A male patient age 72. The patient reports a personal history of cancer. Few moles overall by the patient's own estimate. The patient says their skin reddens with sun exposure. A dermoscopy image of a skin lesion. Acquired for a research image collection, with no referral diagnosis: 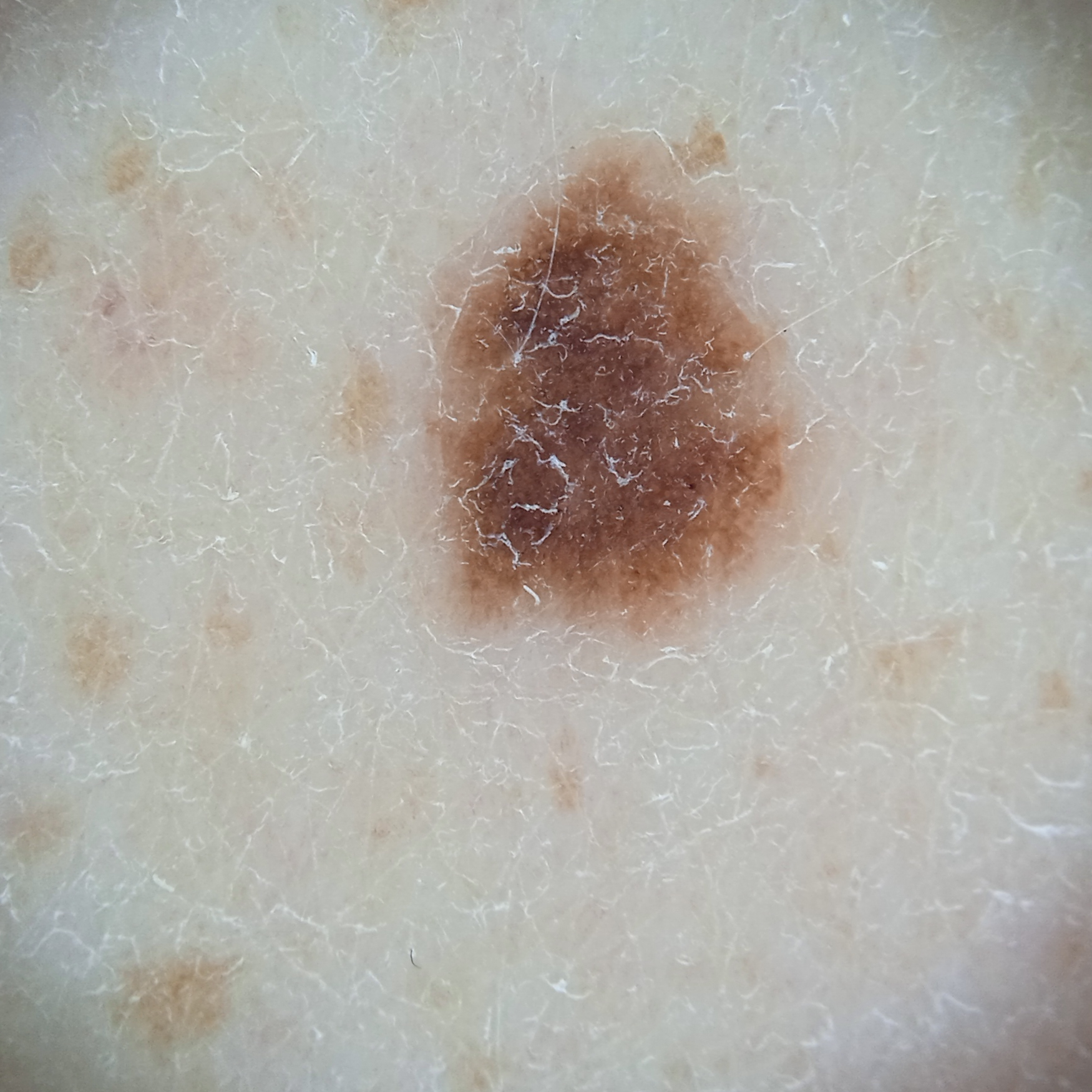anatomic site=the back | diagnosis=melanocytic nevus (dermatologist consensus).